The leg is involved · the patient is a female aged 50–59 · an image taken at an angle.
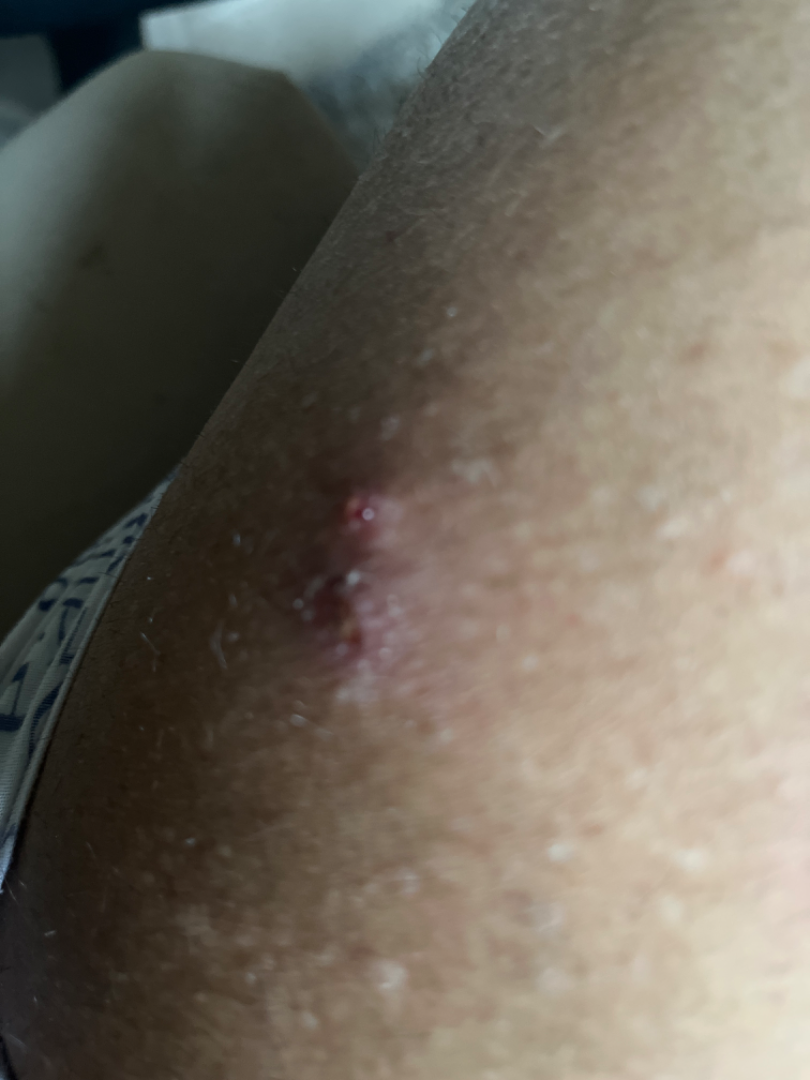The condition could not be reliably identified from the image.